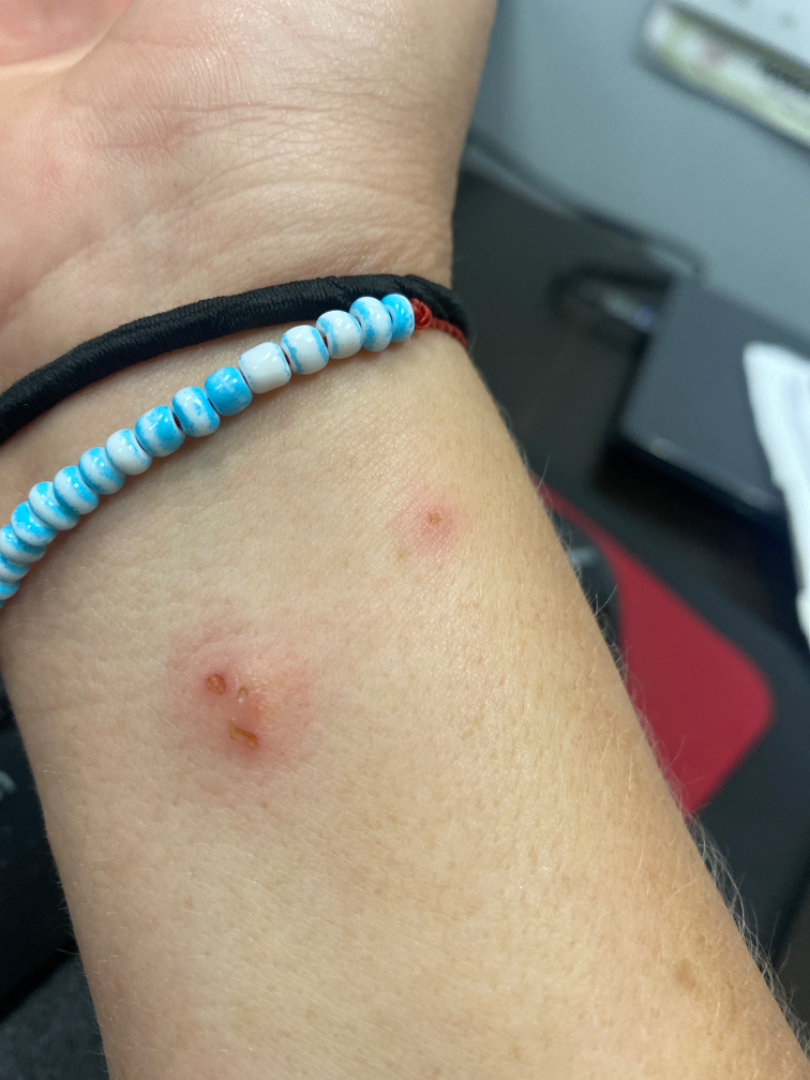lesion texture: raised or bumpy | onset: less than one week | reported symptoms: itching | patient's own categorization: a rash | shot type: close-up | site: arm | assessment: Impetigo (considered); Molluscum Contagiosum (considered); Insect Bite (less likely).